The patient is 18–29, female · the lesion involves the arm · the photograph was taken at an angle — 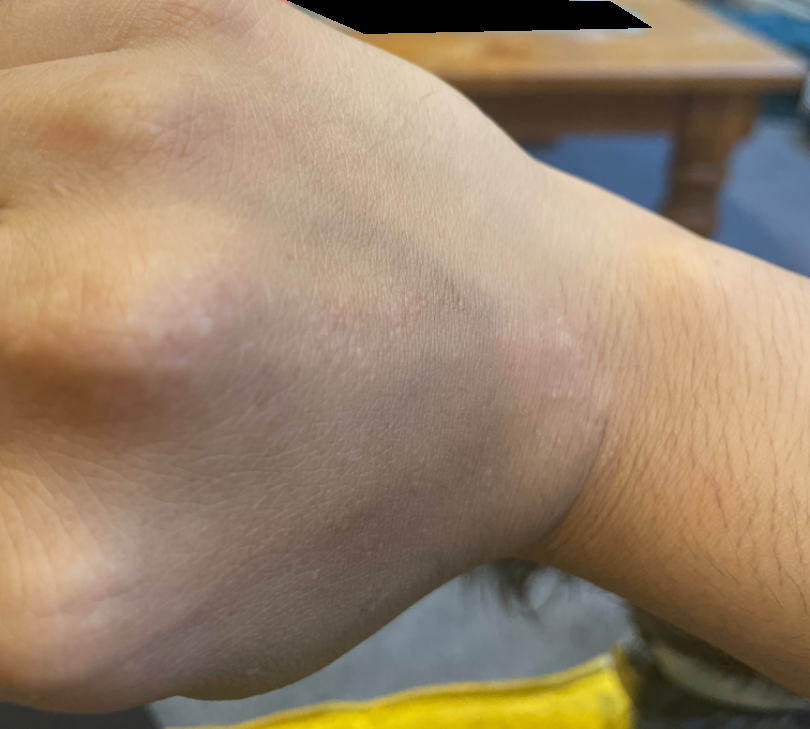diagnostic considerations=three dermatologists each reviewed the case: the differential is split between Verruca vulgaris and Lichen planus/lichenoid eruption; less likely is Lichen nitidus; less probable is Skin hypopigmented; a more distant consideration is Chronic dermatitis, NOS; lower on the differential is Eczema.